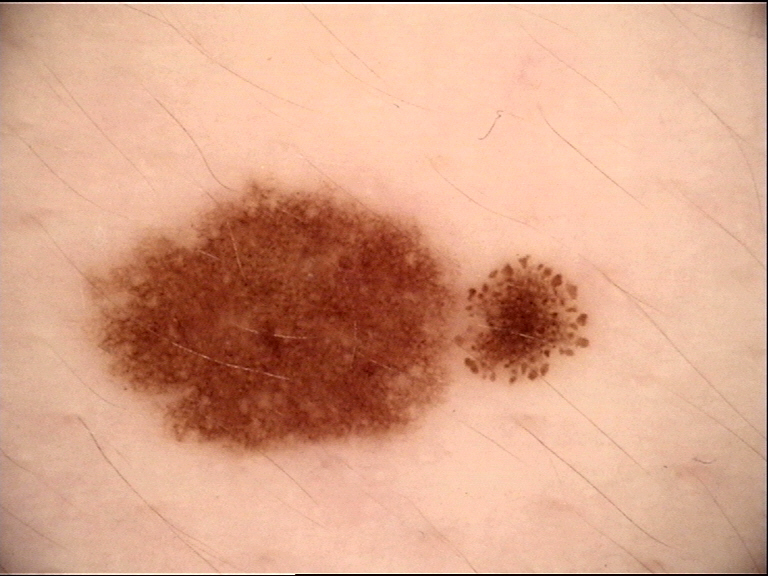{"image": "dermoscopy", "diagnosis": {"name": "dysplastic junctional nevus", "code": "jd", "malignancy": "benign", "super_class": "melanocytic", "confirmation": "expert consensus"}}